Contact-polarized dermoscopy of a skin lesion · a male patient in their mid- to late 40s:
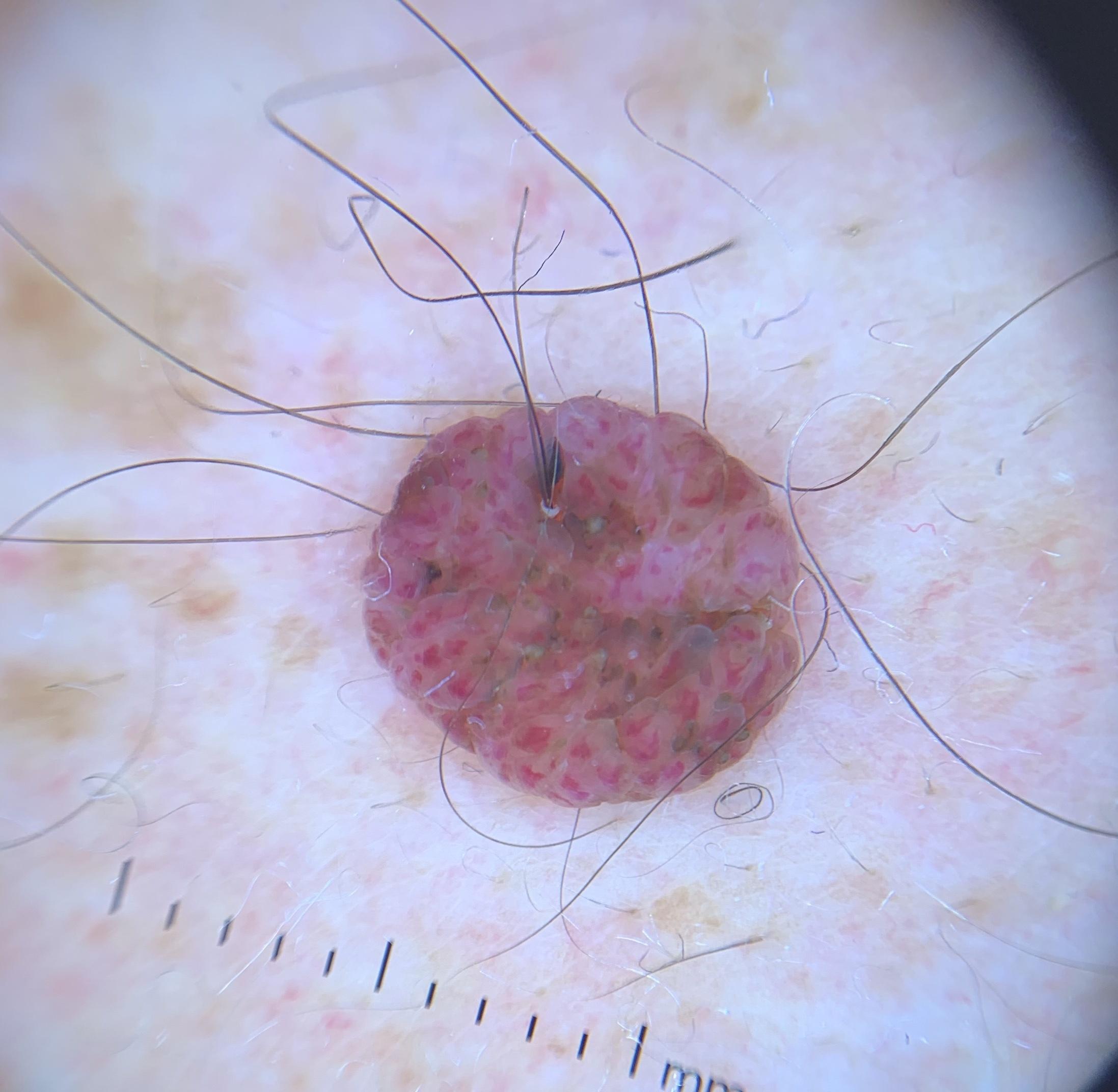body site=the posterior trunk
diagnosis=Nevus (clinical impression)